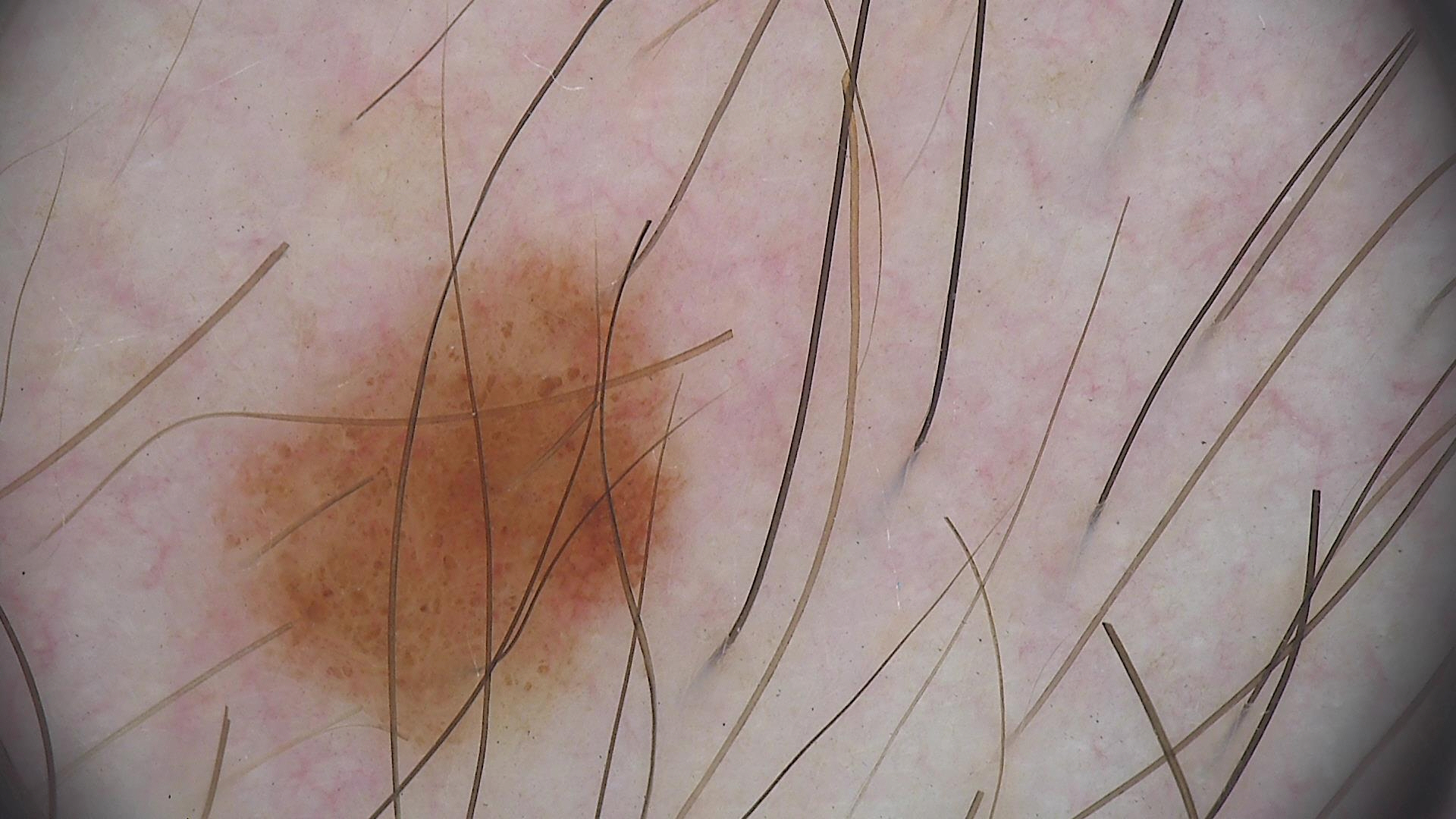Findings:
* class — dysplastic junctional nevus (expert consensus)